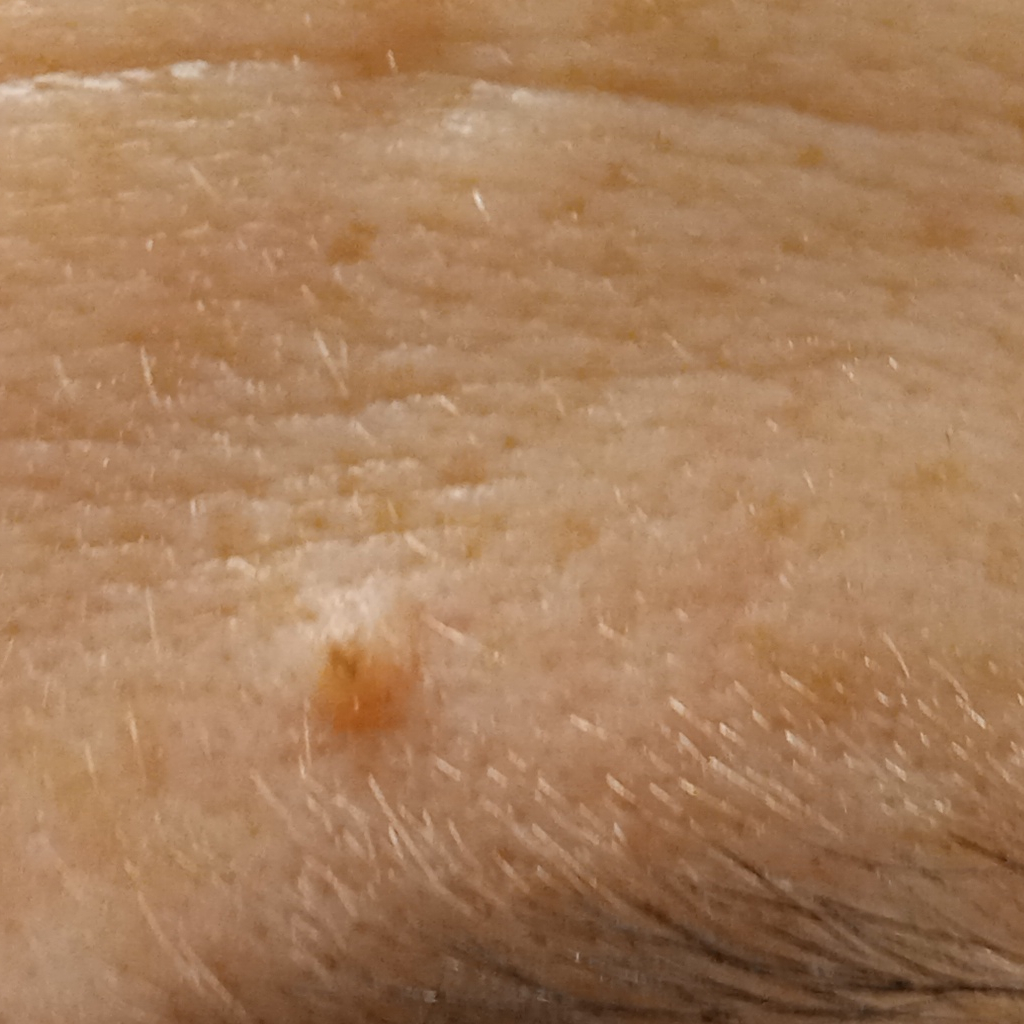Findings:
- subject — female, 50 years of age
- modality — clinical photograph
- referral context — clinical suspicion of melanoma
- body site — the face
- diameter — 1.8 mm
- diagnosis — melanocytic nevus (dermatologist consensus)